A dermoscopy image of a single skin lesion: 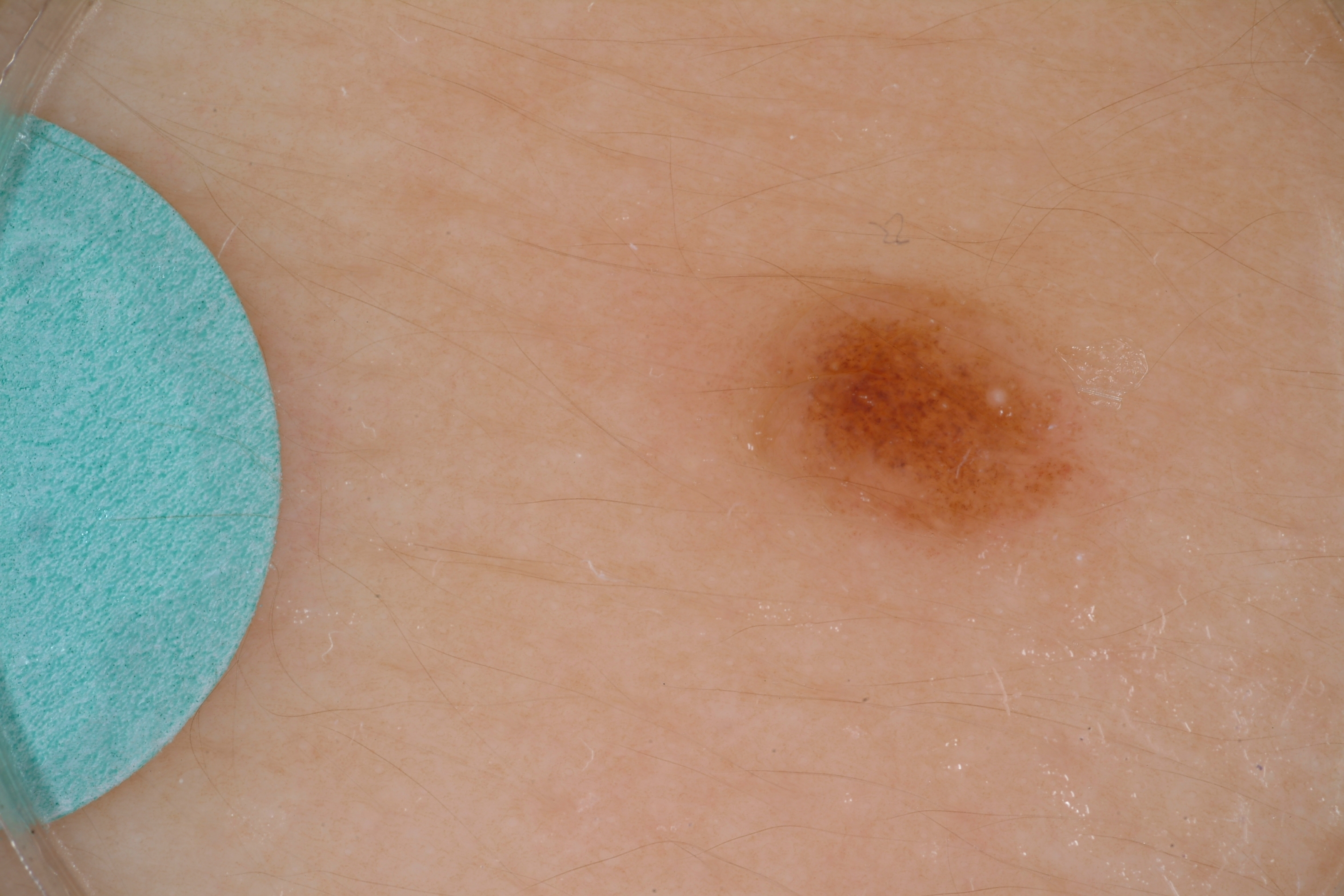Image and clinical context: As (left, top, right, bottom), the visible lesion spans bbox(726, 278, 1095, 539). On dermoscopy, the lesion shows neither streaks nor globules. A small lesion within a wider field of skin. Conclusion: The lesion was assessed as a benign lesion.